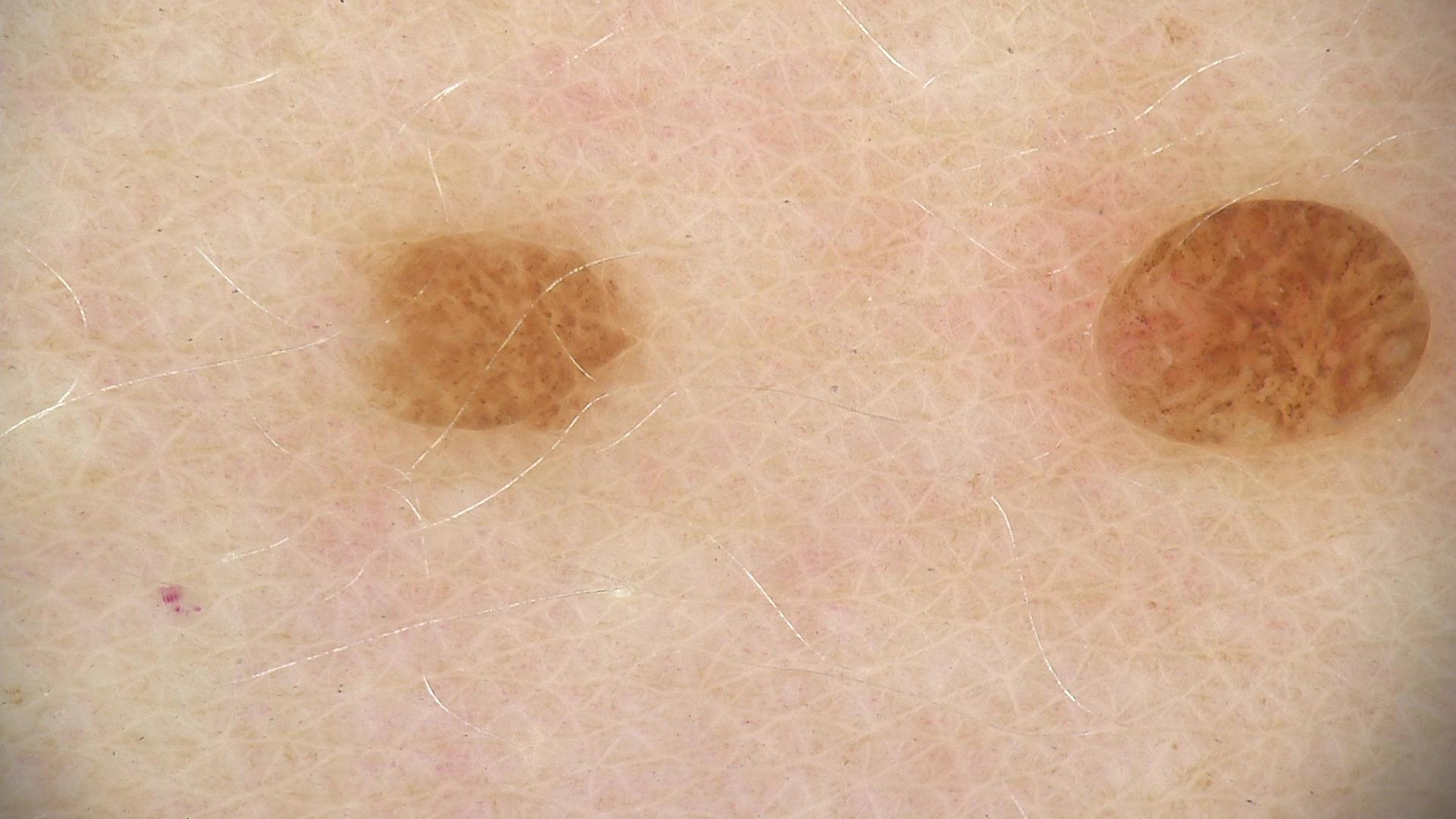{
  "image": "dermatoscopy",
  "lesion_type": {
    "main_class": "banal",
    "pattern": "compound"
  },
  "diagnosis": {
    "name": "compound nevus",
    "code": "cb",
    "malignancy": "benign",
    "super_class": "melanocytic",
    "confirmation": "expert consensus"
  }
}